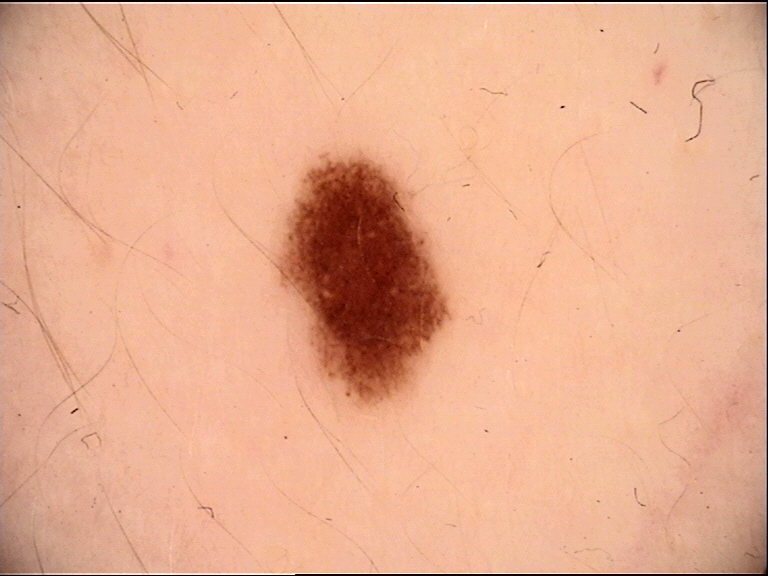Case:
* image — dermoscopy
* label — dysplastic junctional nevus (expert consensus)